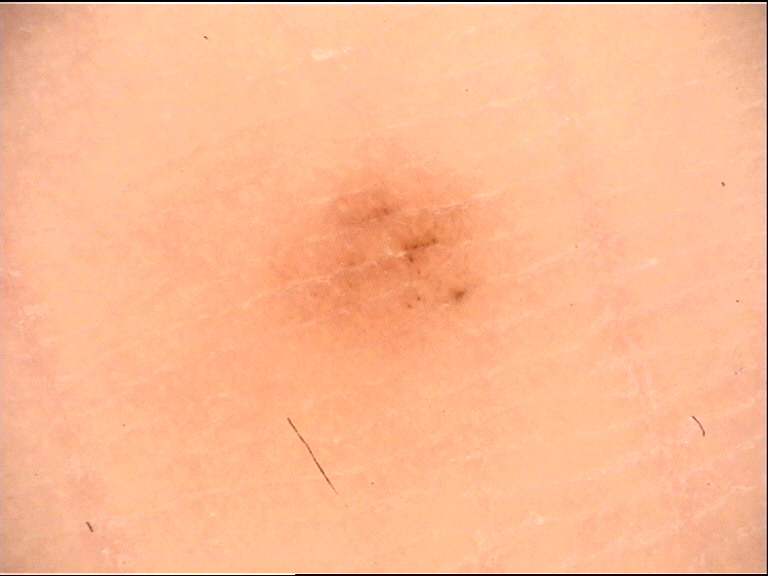Labeled as an acral junctional nevus.